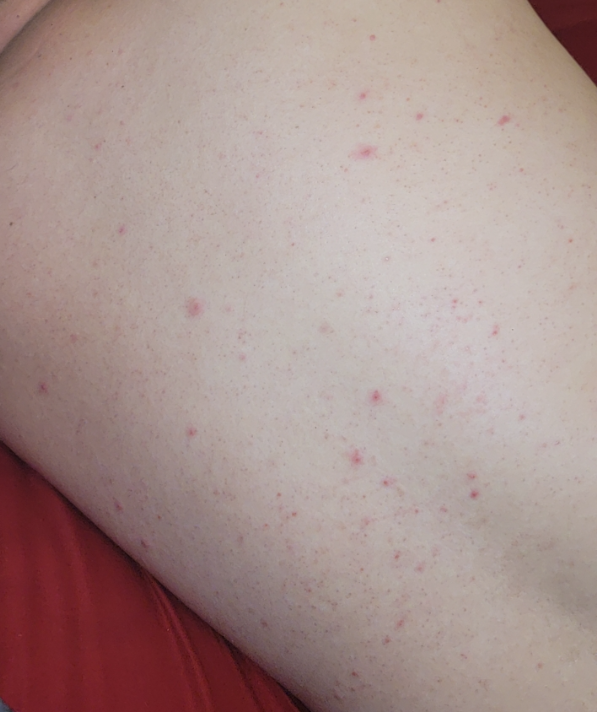diagnostic considerations — reviewed remotely by one dermatologist: the primary impression is Folliculitis; possibly Acne.